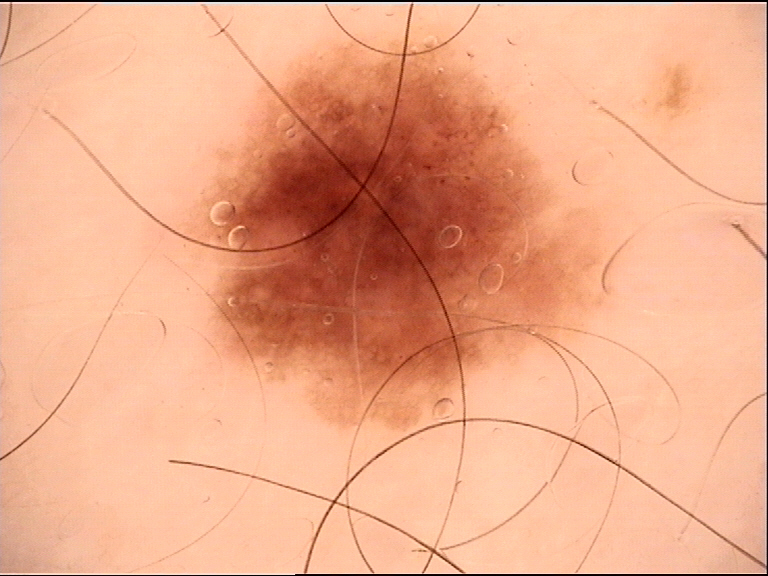A dermoscopic close-up of a skin lesion. Classified as a benign lesion — a dysplastic junctional nevus.